A male patient age 66. Acquired for a research image collection, with no referral diagnosis. Dermoscopy of a skin lesion — 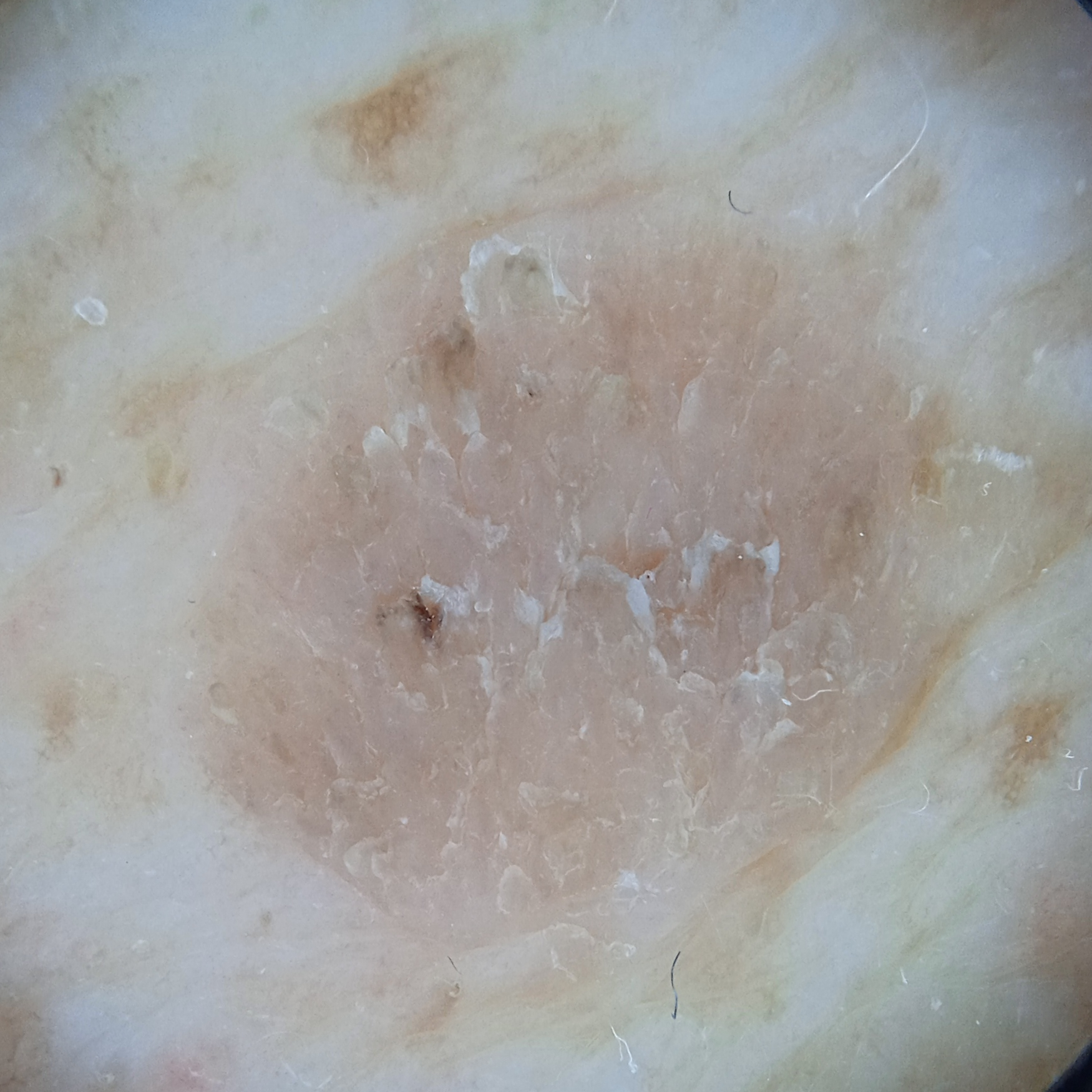Located on the back.
Measuring roughly 9.5 mm.
The diagnostic impression was a seborrheic keratosis.